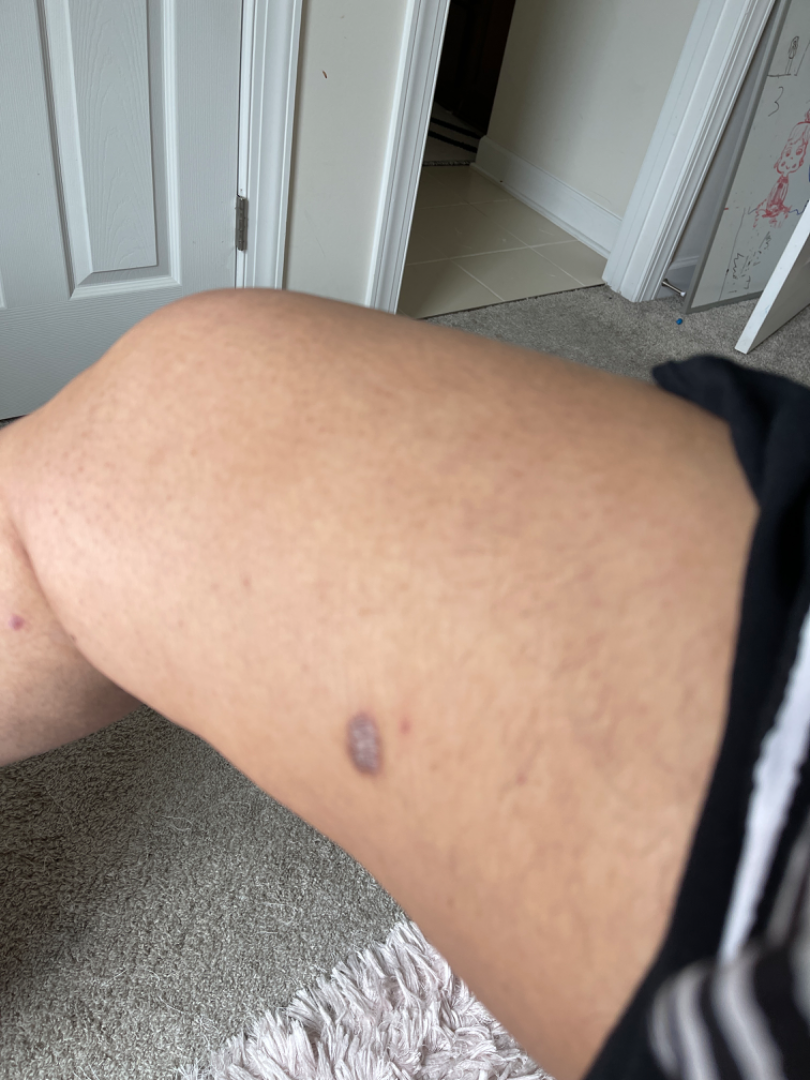Q: Patient's own categorization?
A: a rash
Q: Any systemic symptoms?
A: none reported
Q: When did this start?
A: three to twelve months
Q: Fitzpatrick or Monk tone?
A: Fitzpatrick phototype III; lay reviewers estimated MST 3 or 5
Q: What symptoms does the patient report?
A: bothersome appearance
Q: What is the framing?
A: at a distance
Q: What conditions are considered?
A: Dermatofibroma (possible); SK/ISK (possible); Melanoma (remote)